This is a close-up image · located on the back of the hand and arm — 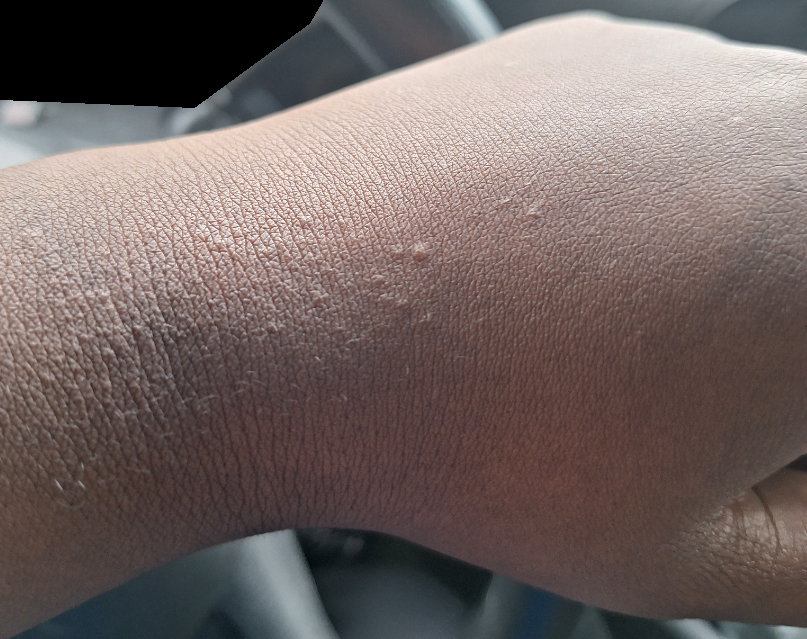Background:
Texture is reported as raised or bumpy. The condition has been present for about one day. Self-categorized by the patient as a rash.
Findings:
On photographic review by a dermatologist: Chronic dermatitis, NOS (weight 1.00).